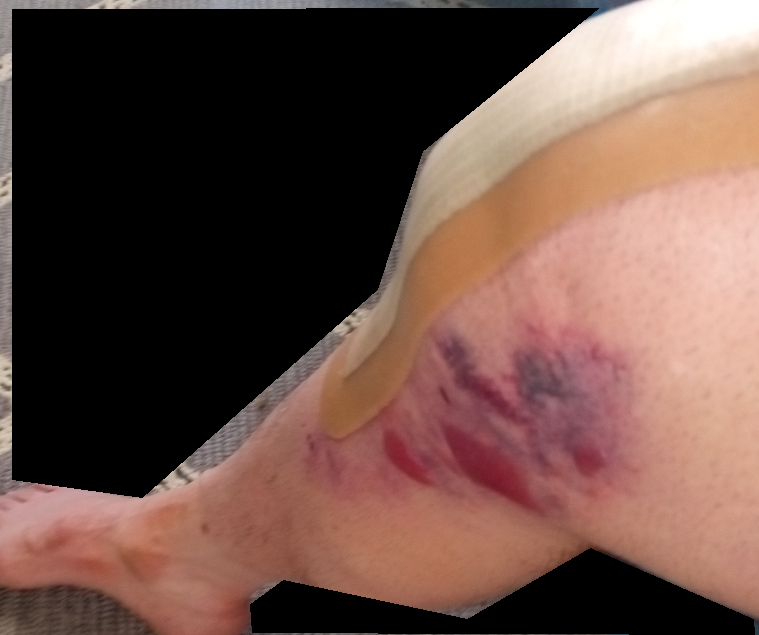assessment: unable to determine | anatomic site: leg | image framing: at a distance | contributor: male, age 60–69.